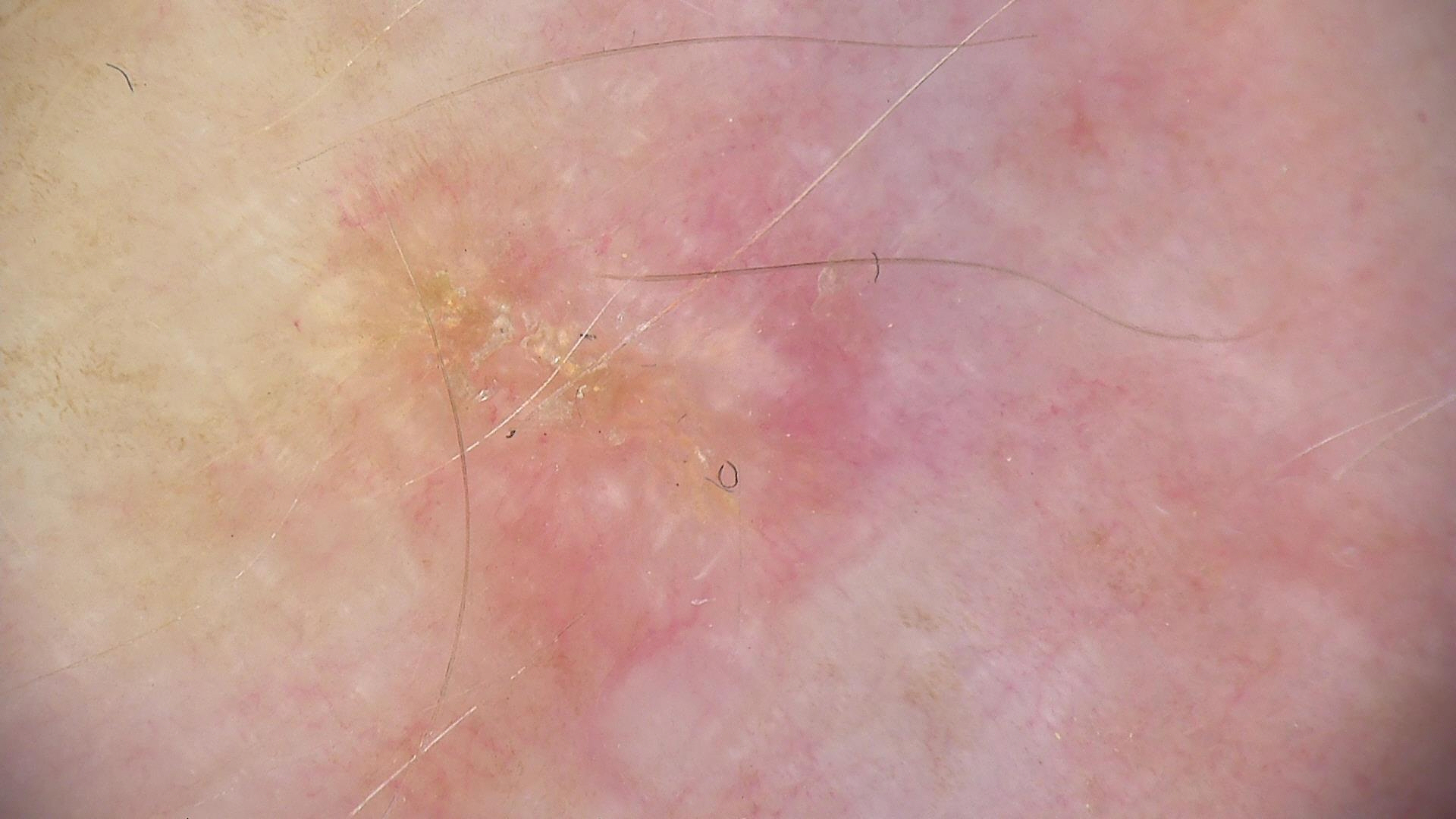A dermoscopic close-up of a skin lesion.
This is a keratinocytic lesion.
Diagnosed as a lesion with uncertain malignant potential — an actinic keratosis.